A dermoscopic close-up of a skin lesion: 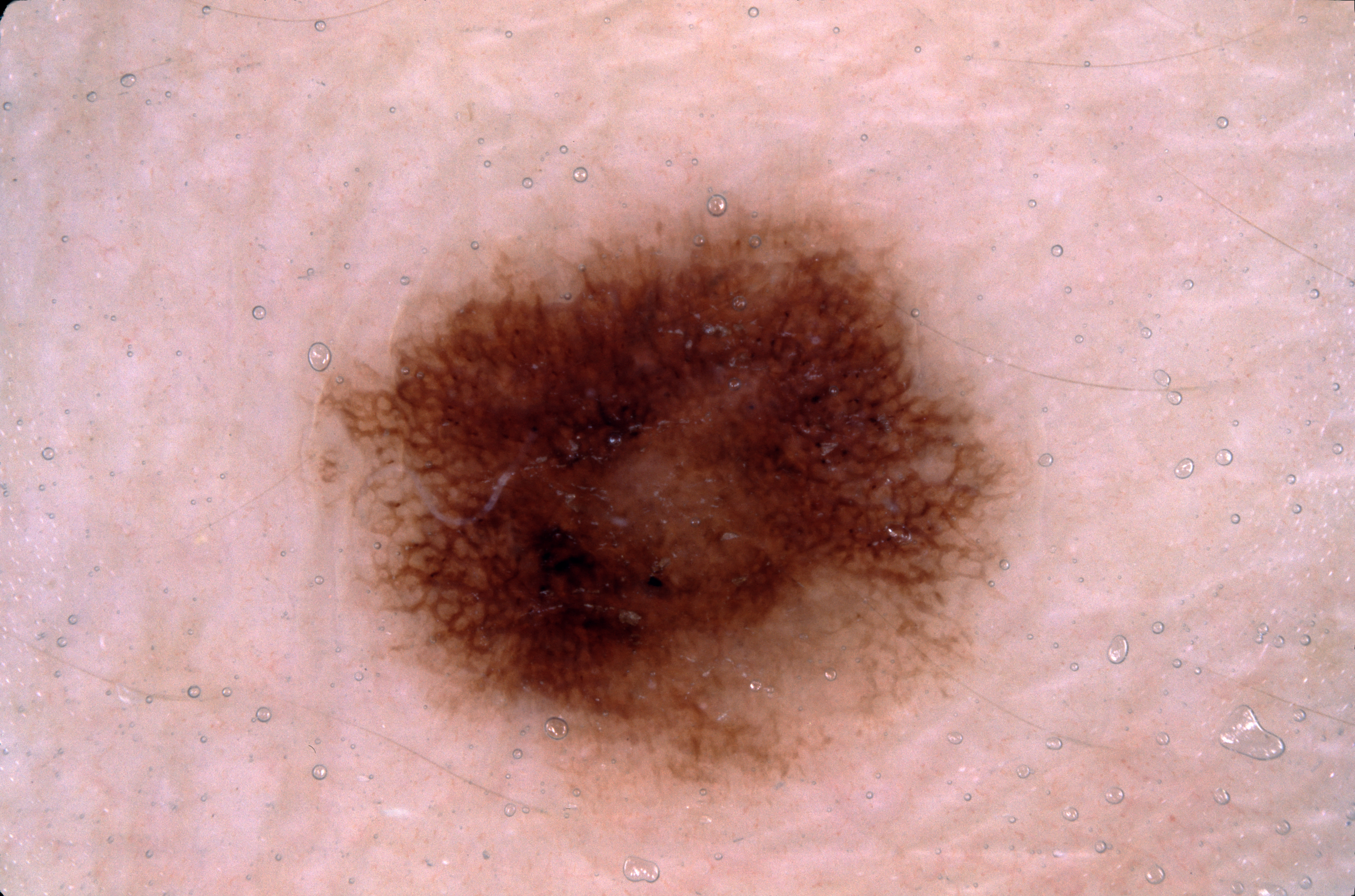<case>
<lesion_location>
  <bbox_xyxy>317, 194, 1018, 796</bbox_xyxy>
</lesion_location>
<dermoscopic_features>
  <present>pigment network</present>
  <absent>streaks, negative network, milia-like cysts</absent>
</dermoscopic_features>
<diagnosis>
  <name>melanocytic nevus</name>
  <malignancy>benign</malignancy>
  <lineage>melanocytic</lineage>
  <provenance>clinical</provenance>
</diagnosis>
</case>